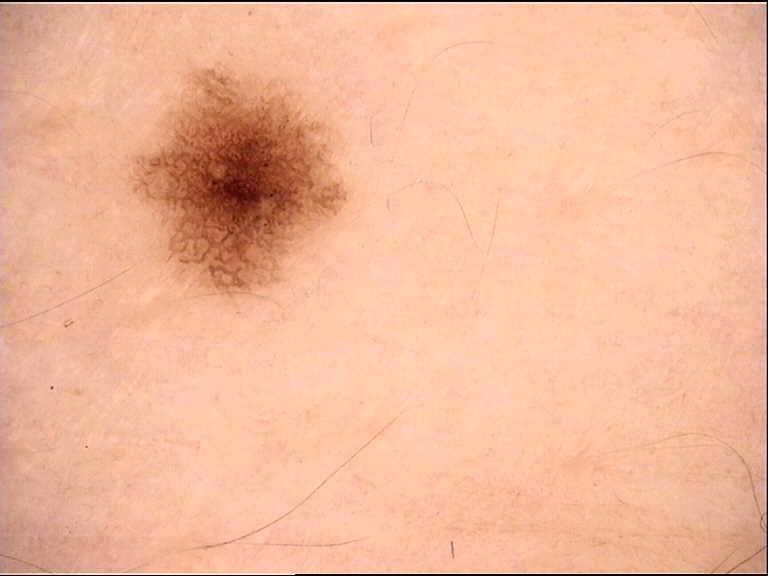  image: dermatoscopy
  diagnosis:
    name: dysplastic junctional nevus
    code: jd
    malignancy: benign
    super_class: melanocytic
    confirmation: expert consensus